A patient in their 80s:
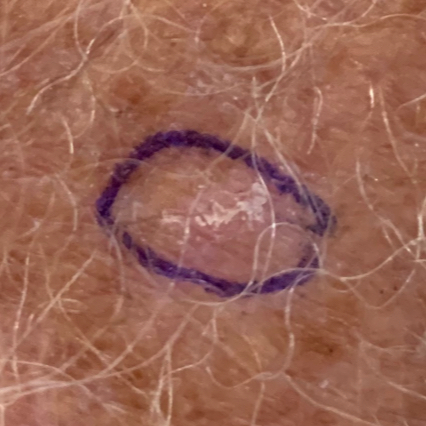  lesion_location: a forearm
  symptoms:
    absent:
      - elevation
      - pain
  diagnosis:
    name: actinic keratosis
    code: ACK
    malignancy: indeterminate
    confirmation: clinical consensus